This image was taken at a distance: 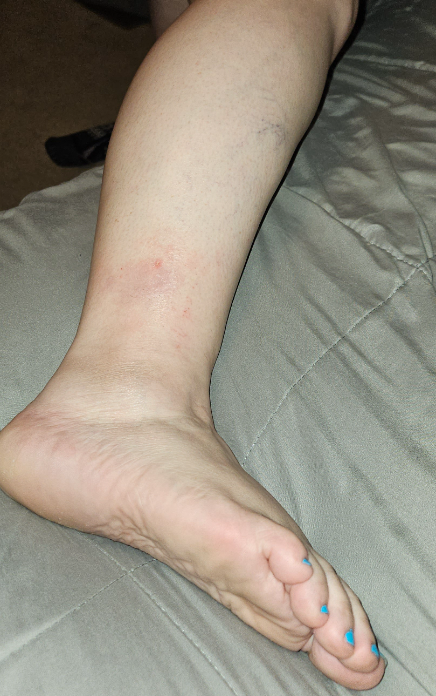On remote review of the image: the favored diagnosis is Stasis Dermatitis; an alternative is Livedoid vasculopathy.